A skin lesion imaged with a dermatoscope.
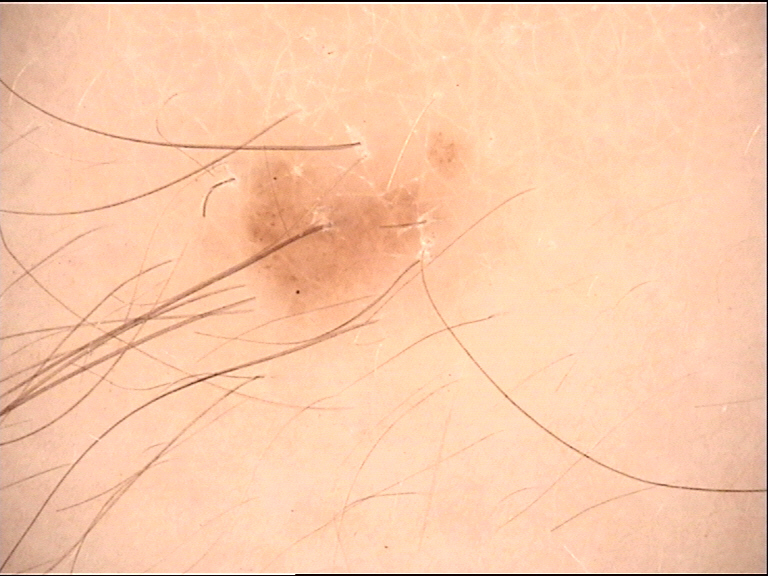{"diagnosis": {"name": "congenital compound nevus", "code": "ccb", "malignancy": "benign", "super_class": "melanocytic", "confirmation": "expert consensus"}}